The patient reports the lesion is raised or bumpy. This is a close-up image. Skin tone: Fitzpatrick phototype II; human graders estimated Monk skin tone scale 1 (US pool) or 2 (India pool) — 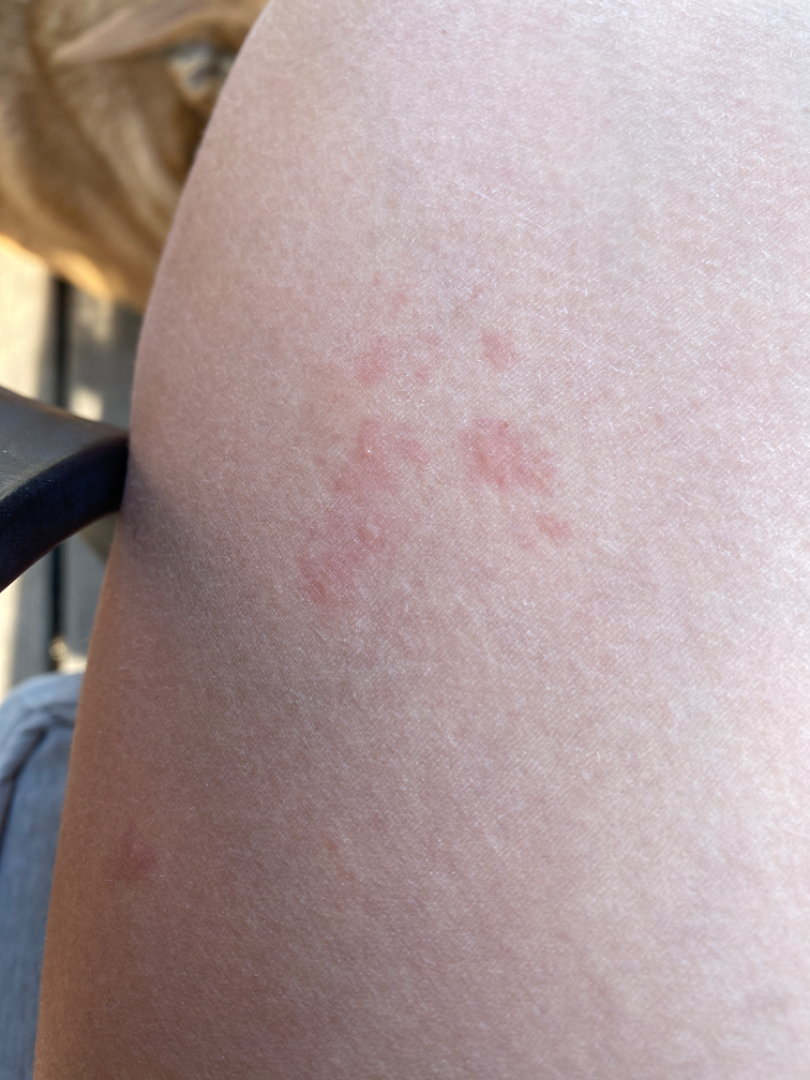Q: Could the case be diagnosed?
A: indeterminate